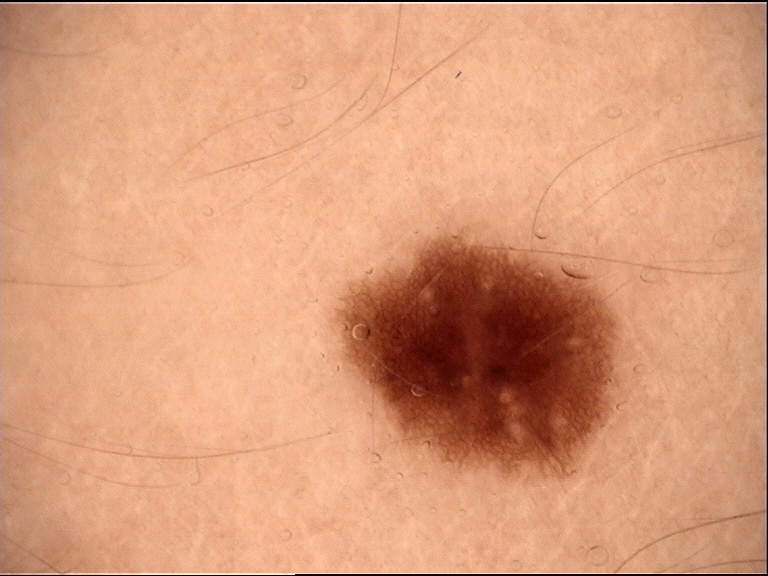label = dysplastic junctional nevus (expert consensus).